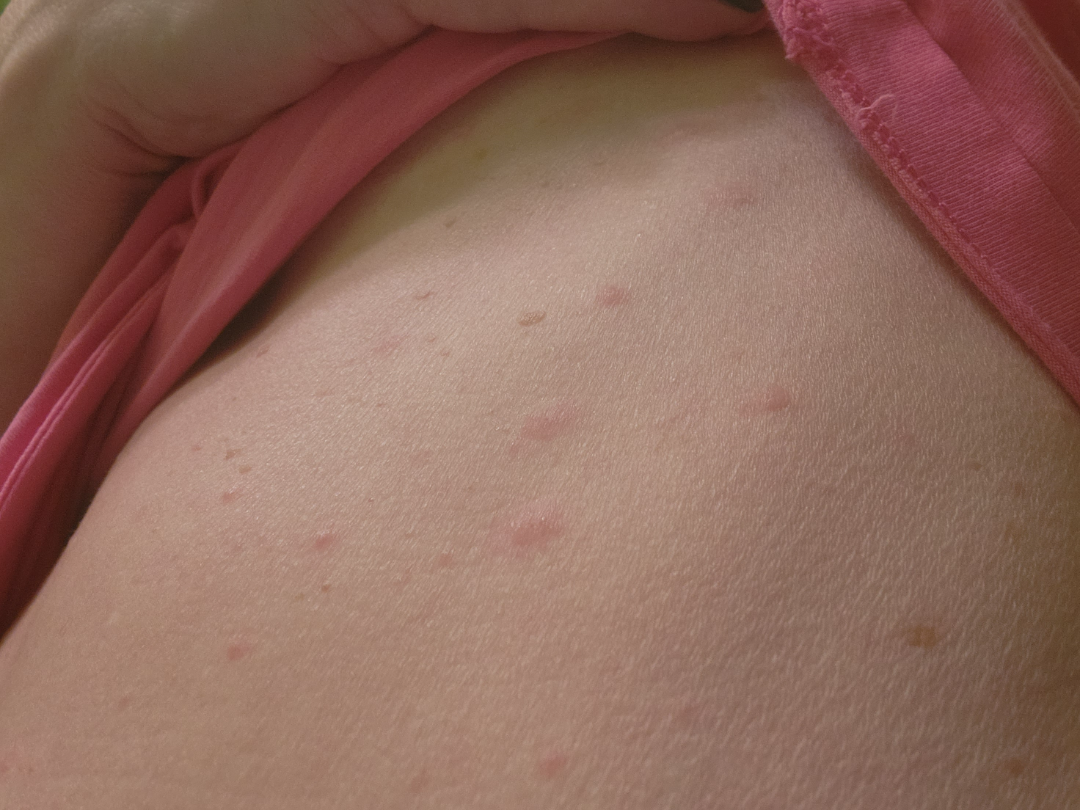On dermatologist assessment of the image: the favored diagnosis is Pityriasis rosea; possibly Insect Bite; a more distant consideration is Psoriasis; less probable is Syphilis; lower on the differential is Eczema.